A skin lesion imaged with a dermatoscope · a male subject about 85 years old or older.
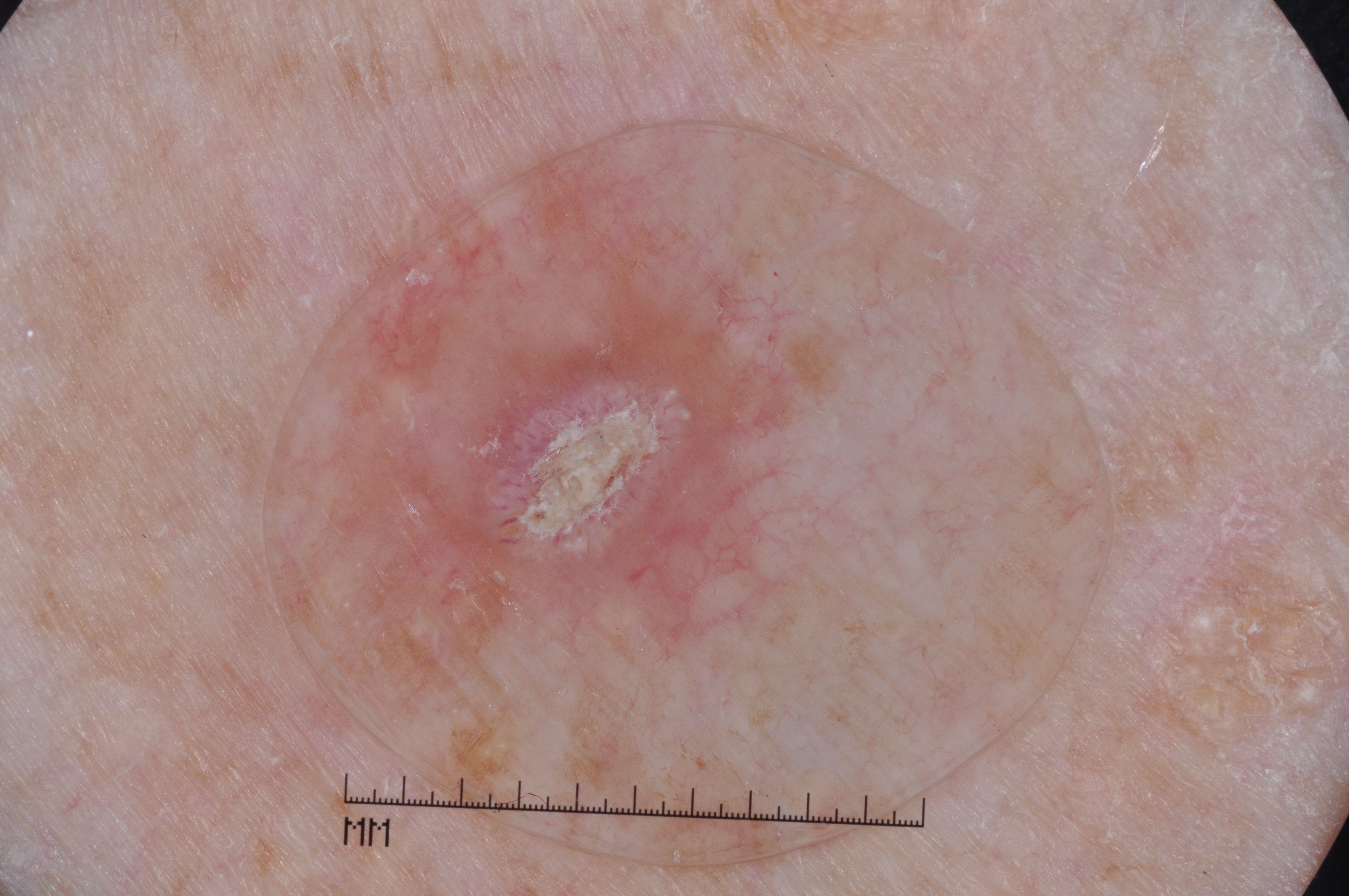Summary: A mid-sized lesion within the field. Dermoscopically, the lesion shows milia-like cysts, with no streaks, negative network, or pigment network. In (x1, y1, x2, y2) order, the lesion is located at <bbox>298, 174, 857, 800</bbox>. Impression: The clinical diagnosis was a seborrheic keratosis, a keratinocytic lesion.